Texture is reported as raised or bumpy. Skin tone: Fitzpatrick phototype II; human graders estimated MST 6 (US pool) or 3 (India pool). Close-up view. Associated systemic symptoms include joint pain. Self-categorized by the patient as a rash. The patient indicates the condition has been present for less than one week. Reported lesion symptoms include itching. The patient is 50–59, female. The palm, back of the torso, front of the torso, arm and back of the hand are involved: 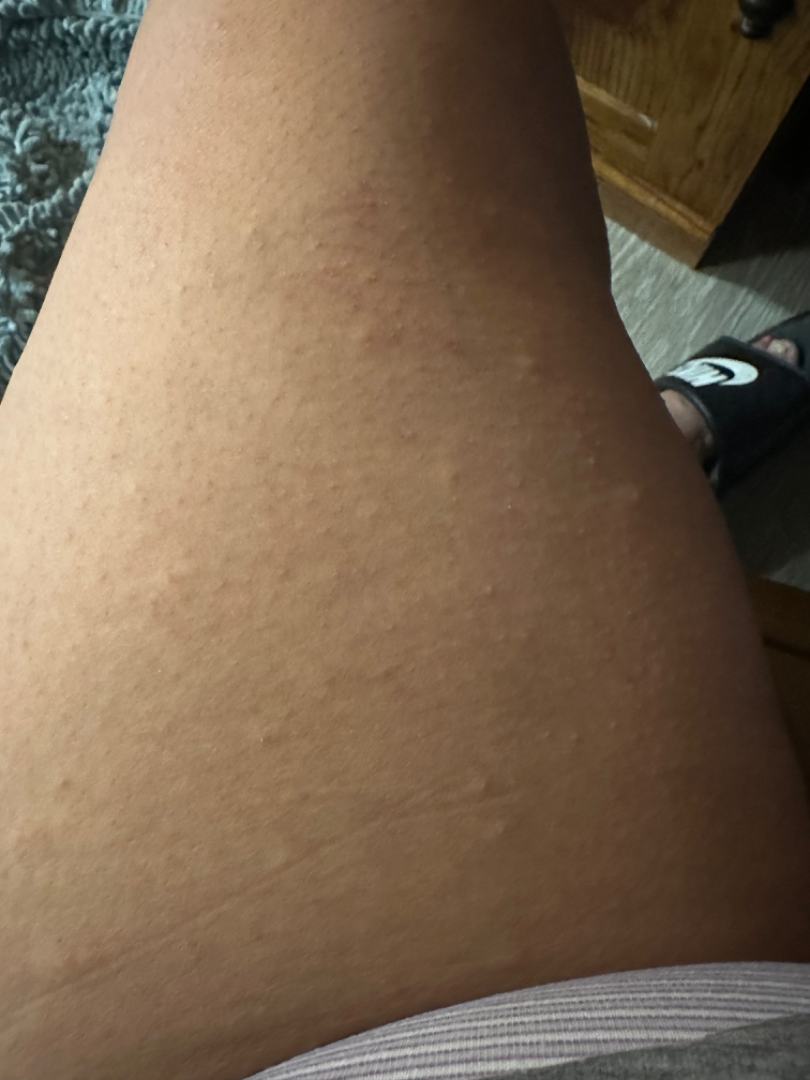On dermatologist assessment of the image: Allergic Contact Dermatitis and Eczema were each considered, in no particular order.